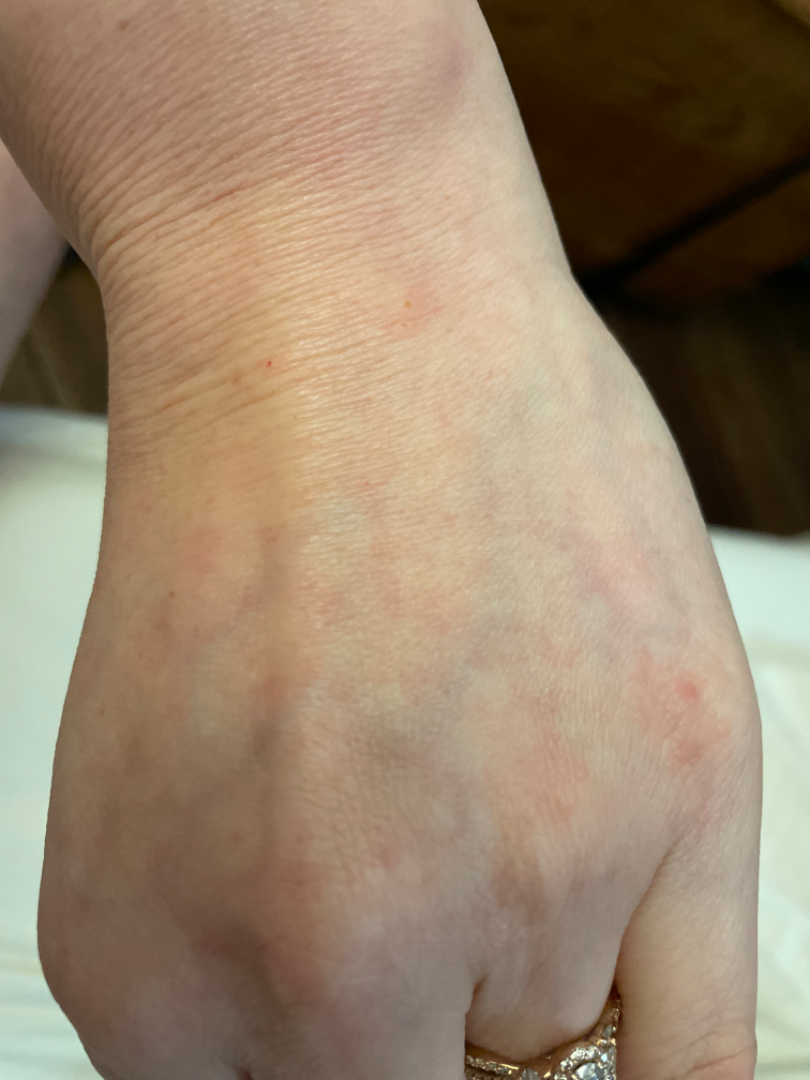Case summary:
* image framing · at an angle
* patient describes the issue as · a rash
* texture · raised or bumpy
* symptoms · itching
* history · less than one week
* differential · consistent with Insect Bite